The lesion involves the head or neck, the photo was captured at a distance, the patient is a male aged 50–59: 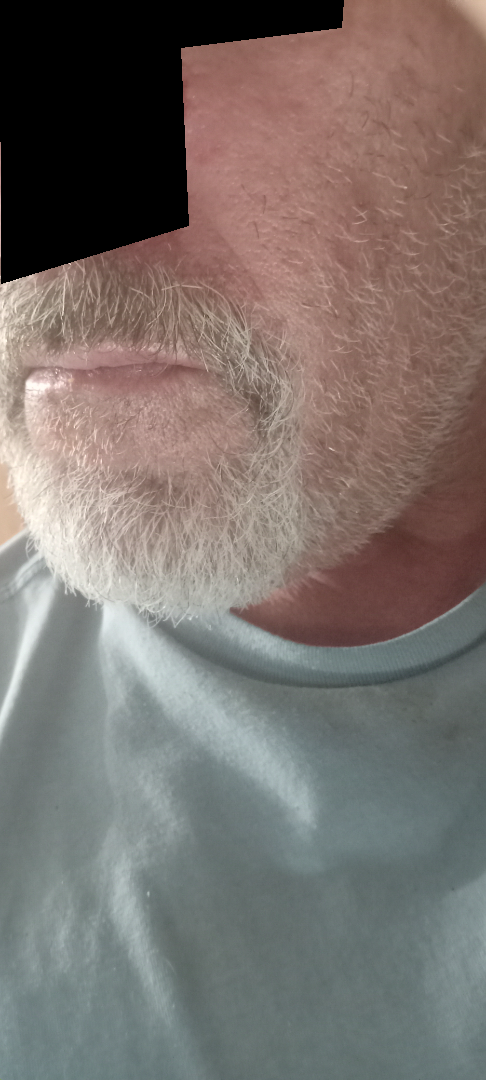assessment=no discernible pathology | lesion texture=raised or bumpy and rough or flaky | associated systemic symptoms=joint pain | symptoms=enlargement.